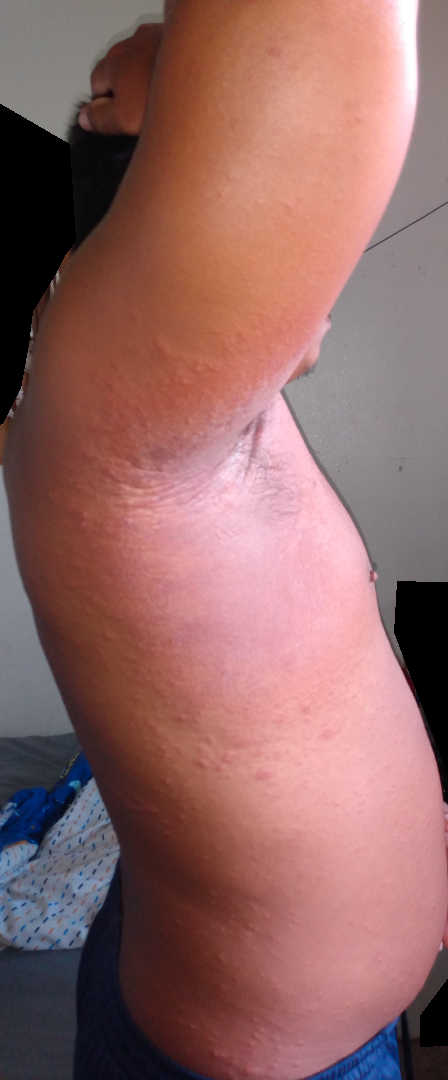<summary>
  <differential>
    <leading>Viral Exanthem</leading>
    <considered>Drug Rash</considered>
    <unlikely>Hypersensitivity</unlikely>
  </differential>
</summary>